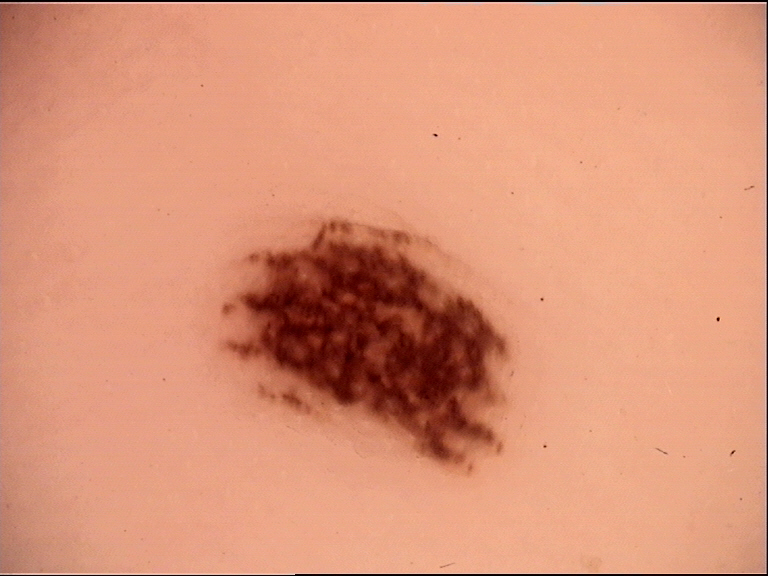A dermoscopic close-up of a skin lesion. Diagnosed as a benign lesion — an acral dysplastic junctional nevus.